This image was taken at an angle — 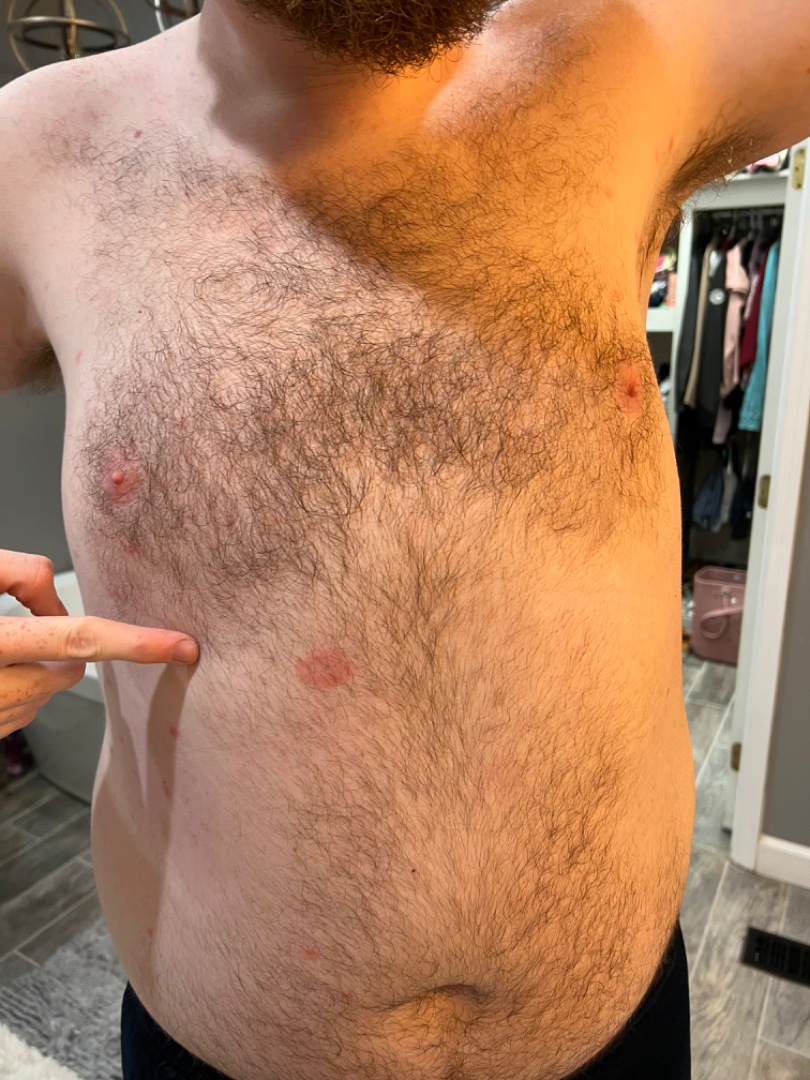assessment: ungradable on photographic review